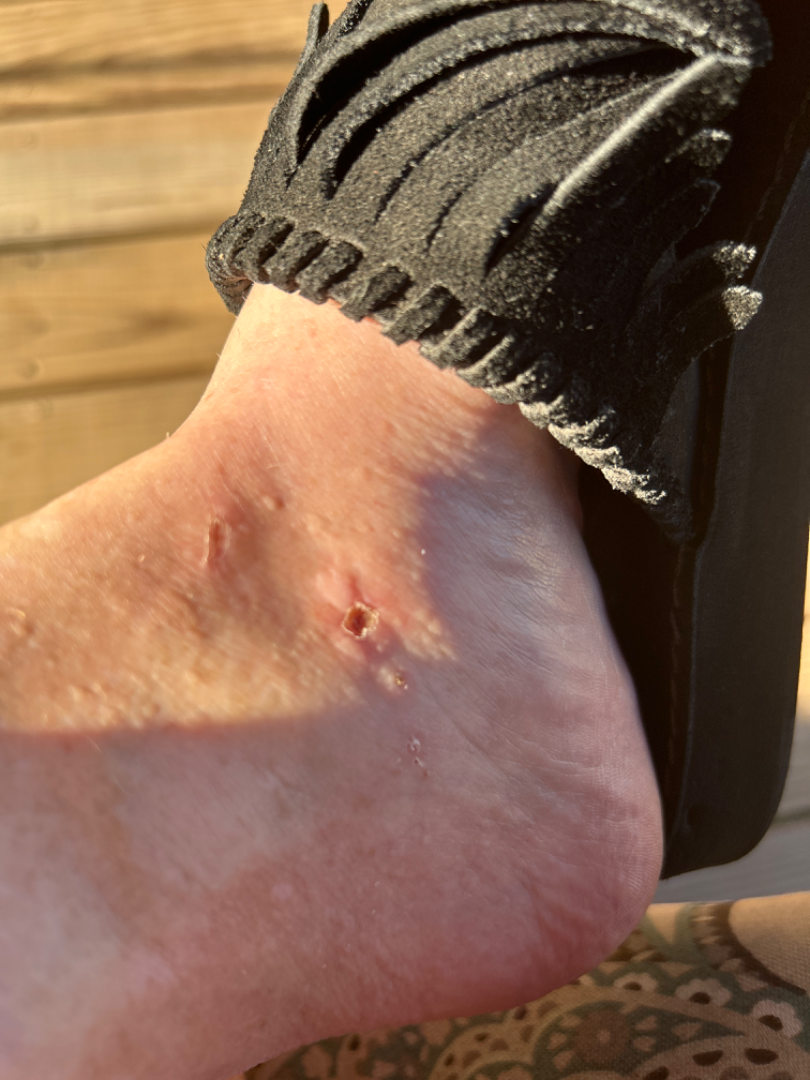The image was not sufficient for the reviewer to characterize the skin condition. The photo was captured at an angle.